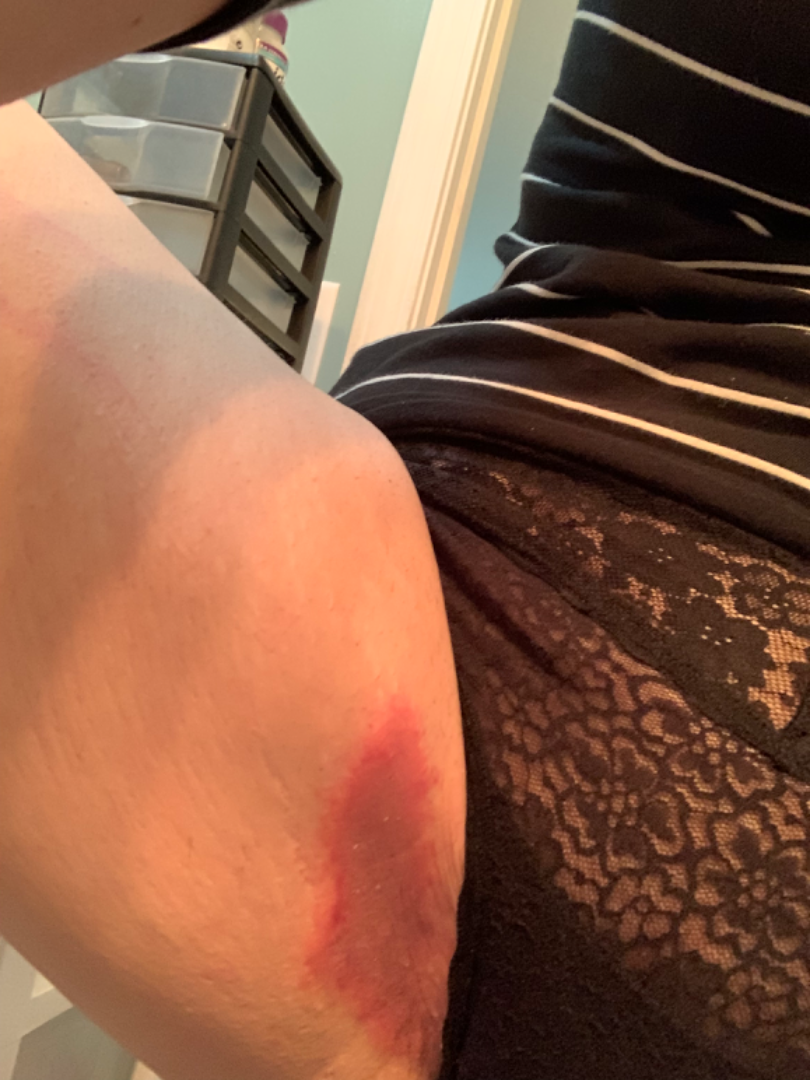Q: Reported symptoms?
A: darkening and bothersome appearance
Q: Who is the patient?
A: female
Q: How was the photo taken?
A: at a distance
Q: Duration?
A: less than one week
Q: What is the patient's skin tone?
A: Fitzpatrick III
Q: What is the affected area?
A: leg
Q: How does the lesion feel?
A: flat and rough or flaky
Q: What is the differential diagnosis?
A: Intertrigo (weight 0.42); Candida intertrigo (weight 0.26); Irritant Contact Dermatitis (weight 0.16); Allergic Contact Dermatitis (weight 0.16)